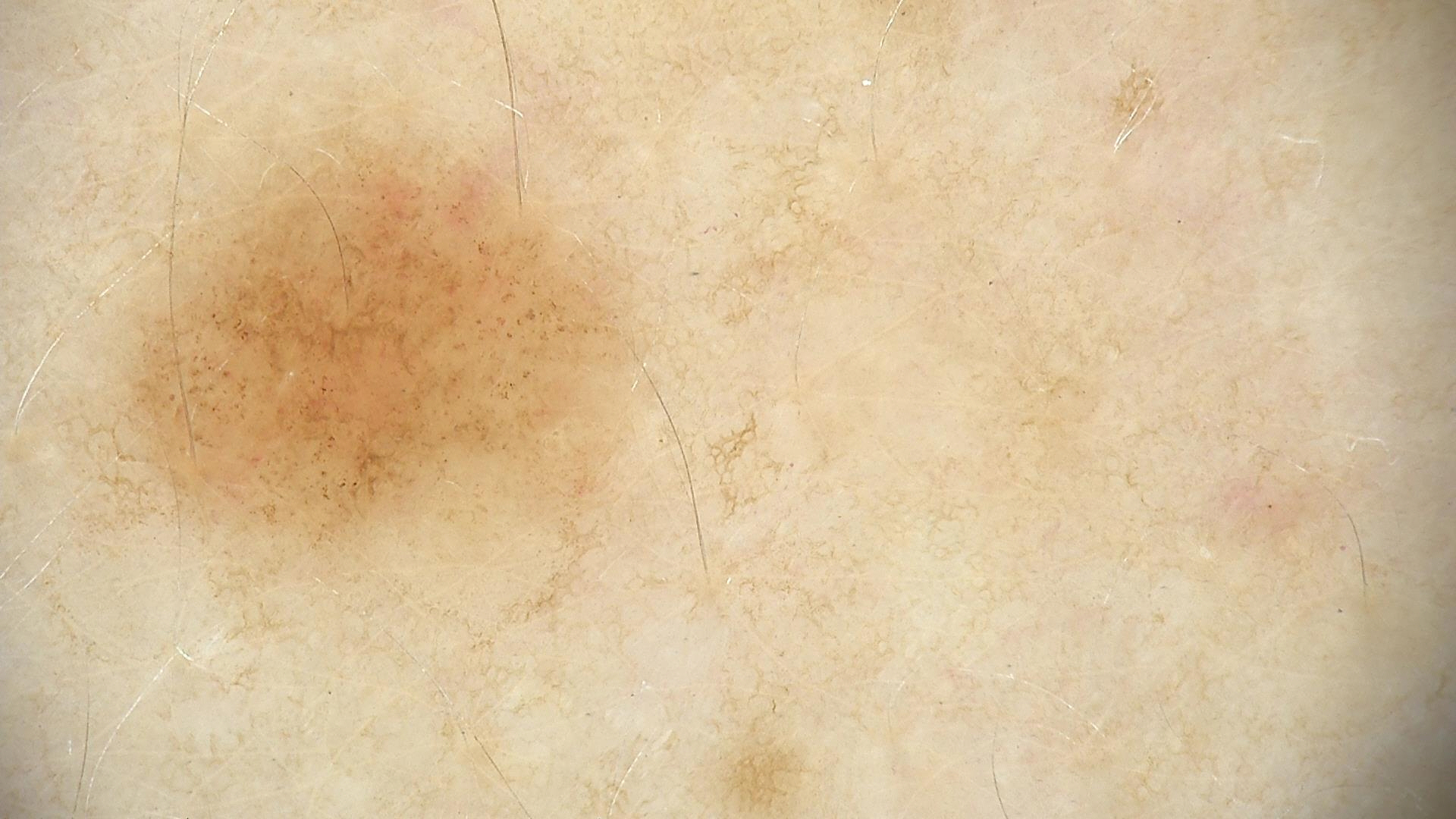A skin lesion imaged with a dermatoscope. Classified as a benign lesion — a dysplastic junctional nevus.